The photo was captured at a distance. The palm and back of the hand are involved. Female subject, age 18–29: 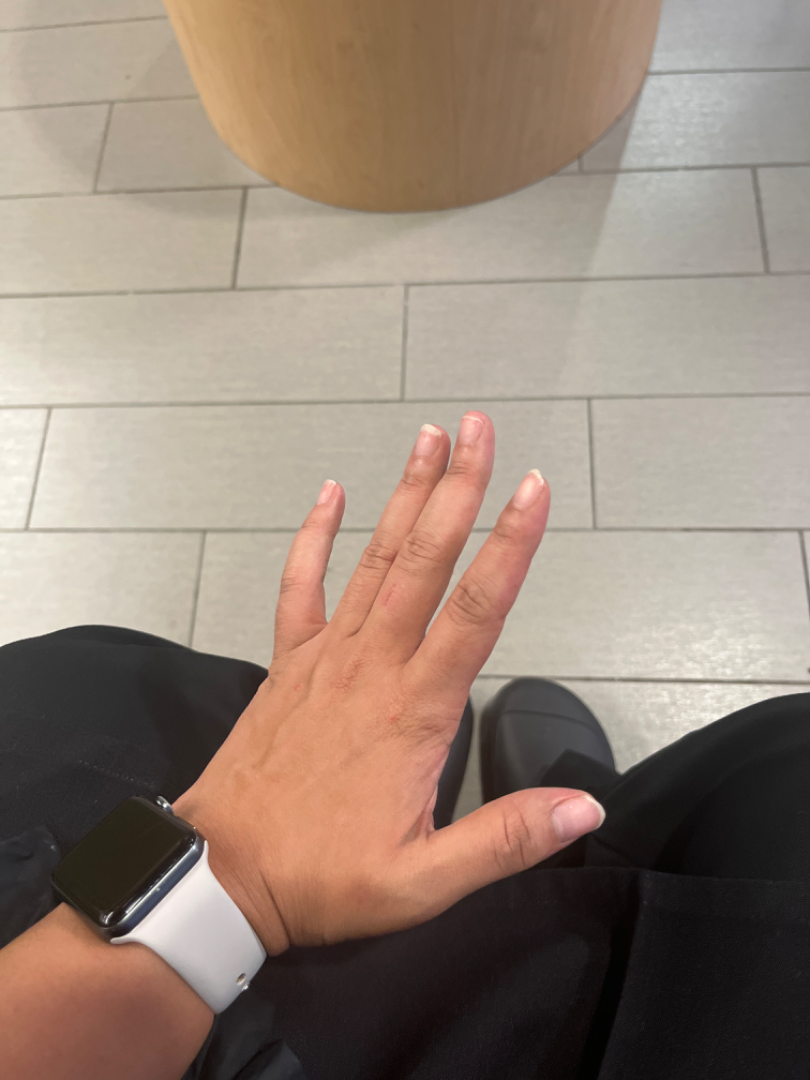  systemic_symptoms:
    - mouth sores
    - fever
  texture: raised or bumpy
  symptoms:
    - bothersome appearance
    - burning
    - pain
  duration: about one day
  differential:
    Eczema: 0.67
    Chilblain: 0.33